The patient described the issue as a rash; the contributor is 40–49, female; the contributor reports itching and bothersome appearance; the lesion involves the leg; reported duration is about one day; this image was taken at a distance; skin tone: Fitzpatrick skin type II:
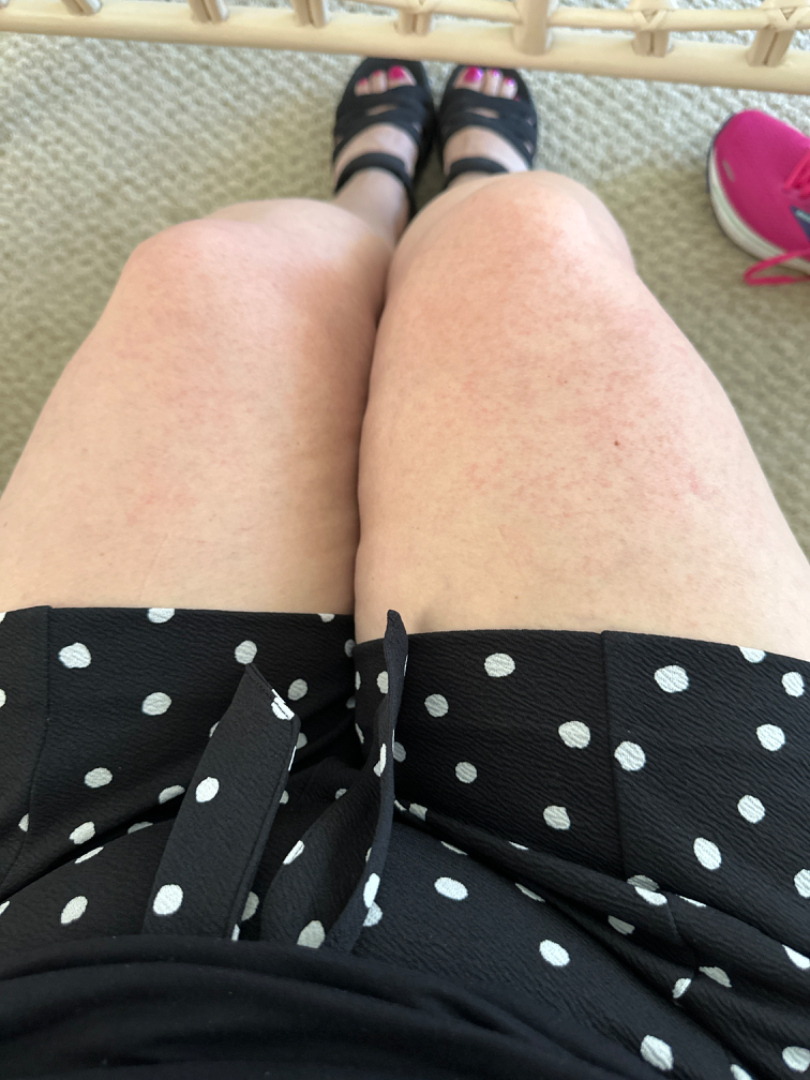On photographic review: the leading consideration is Keratosis pilaris; also consider Folliculitis; also on the differential is Eczema.